A clinical photograph of a skin lesion; a male patient aged 73-77:
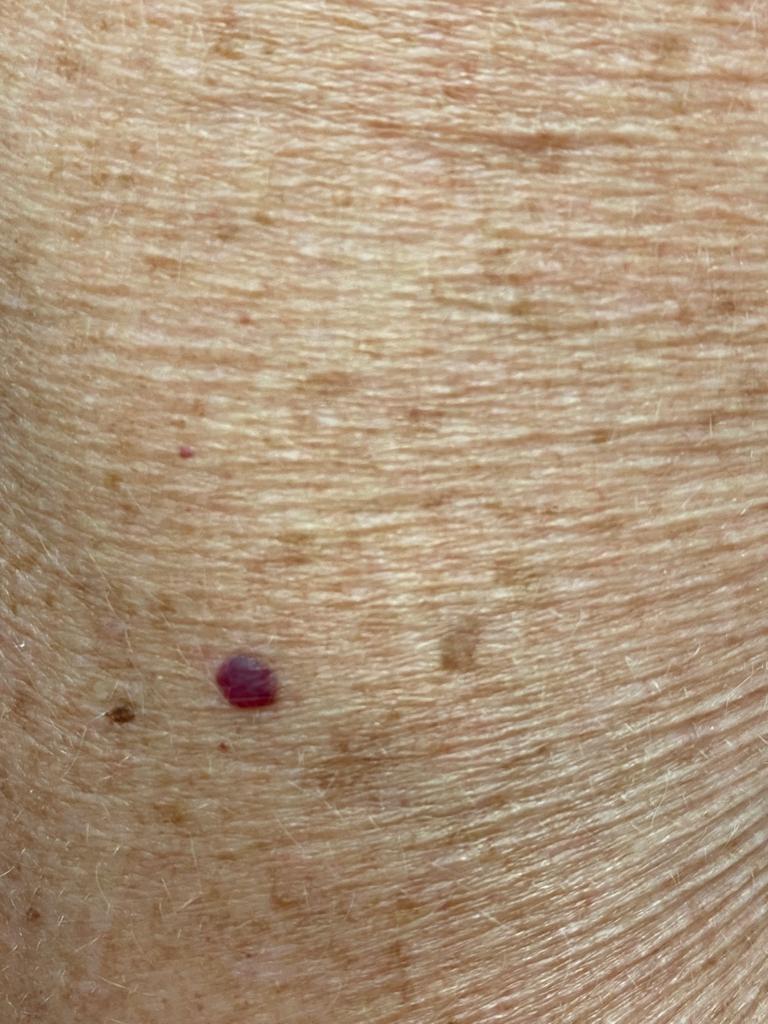The lesion is located on the trunk (the posterior trunk). Consistent with a vascular lesion.